Reported lesion symptoms include burning · self-categorized by the patient as skin that appeared healthy to them · the lesion involves the leg · present for about one day · texture is reported as raised or bumpy · a close-up photograph · the patient is a male aged 50–59 · FST III; lay reviewers estimated a Monk skin tone scale of 2: 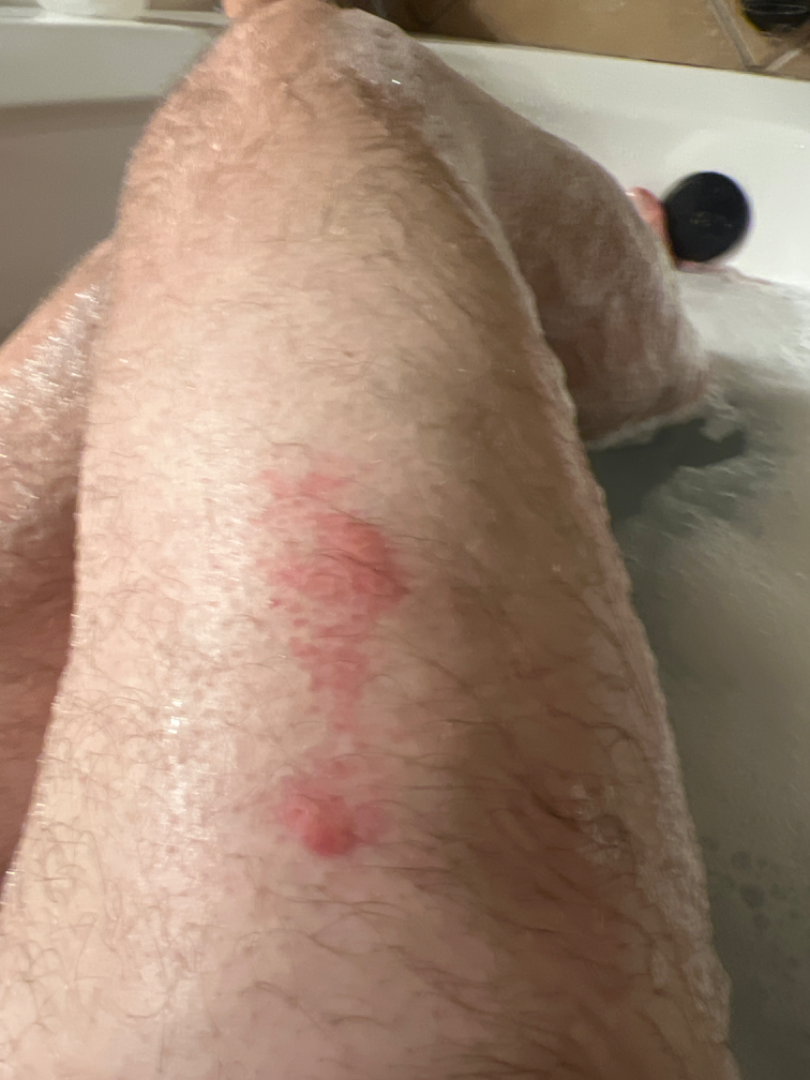Q: What is the differential diagnosis?
A: reviewed remotely by one dermatologist: most likely Allergic Contact Dermatitis; also raised was Insect Bite; a remote consideration is Eczema